A moderate number of moles by the patient's own estimate · acquired for a research image collection, with no referral diagnosis · a dermatoscopic image of a skin lesion · the patient says their skin tans without first burning.
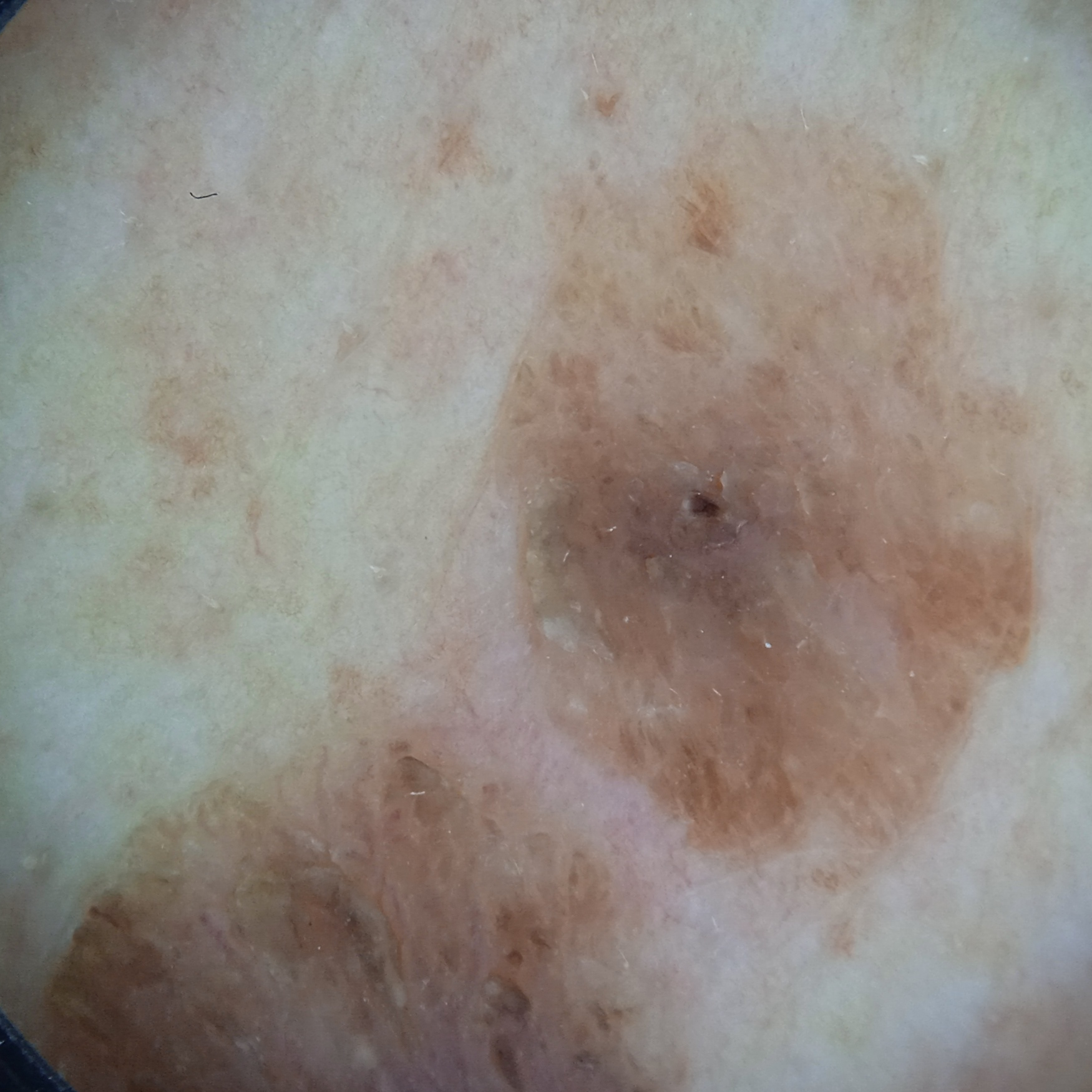Clinical context: The lesion involves the back. The lesion measures approximately 12.8 mm. Conclusion: The diagnostic impression was a seborrheic keratosis.